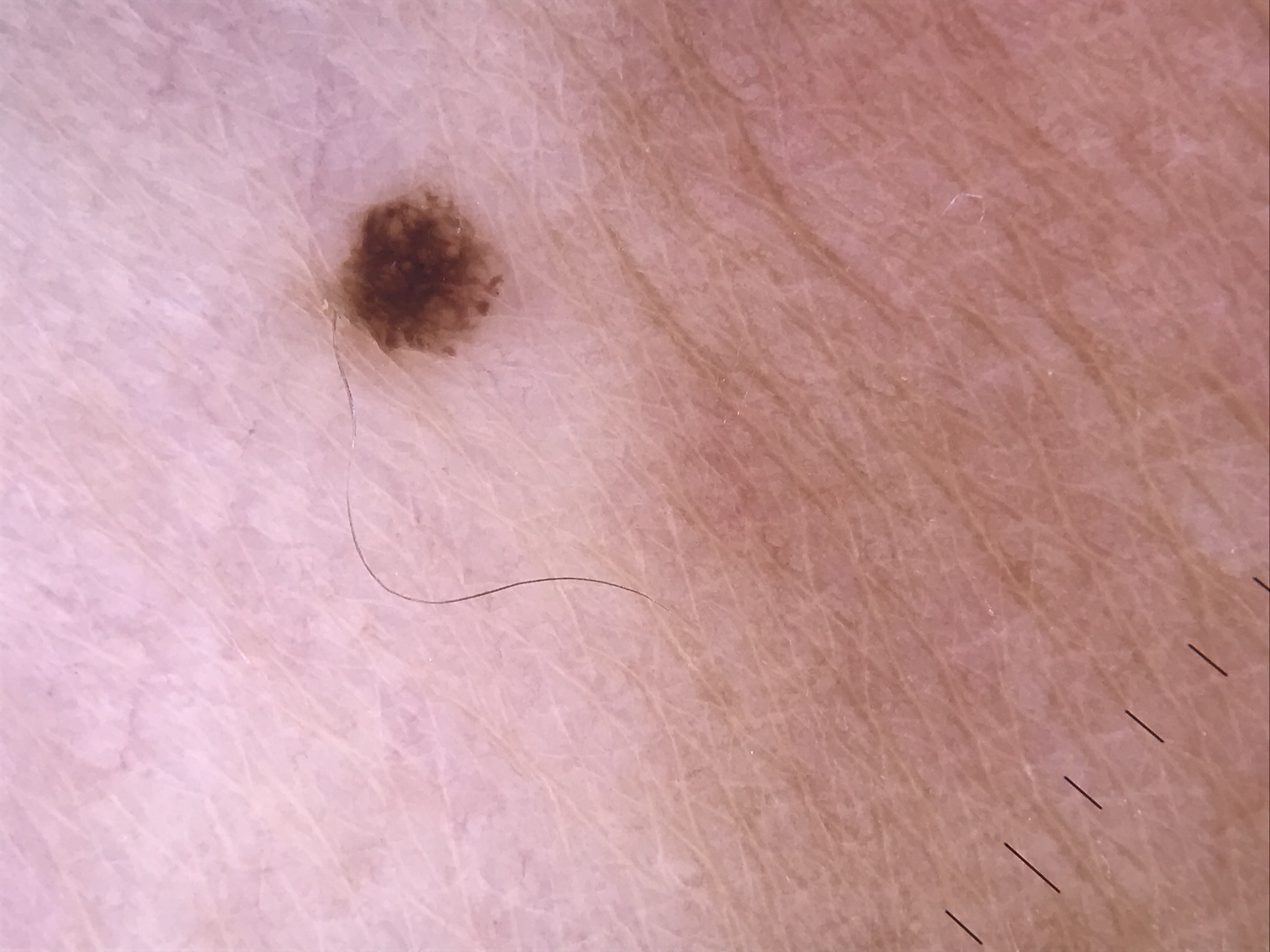| feature | finding |
|---|---|
| imaging | dermoscopy |
| class | dysplastic junctional nevus (expert consensus) |